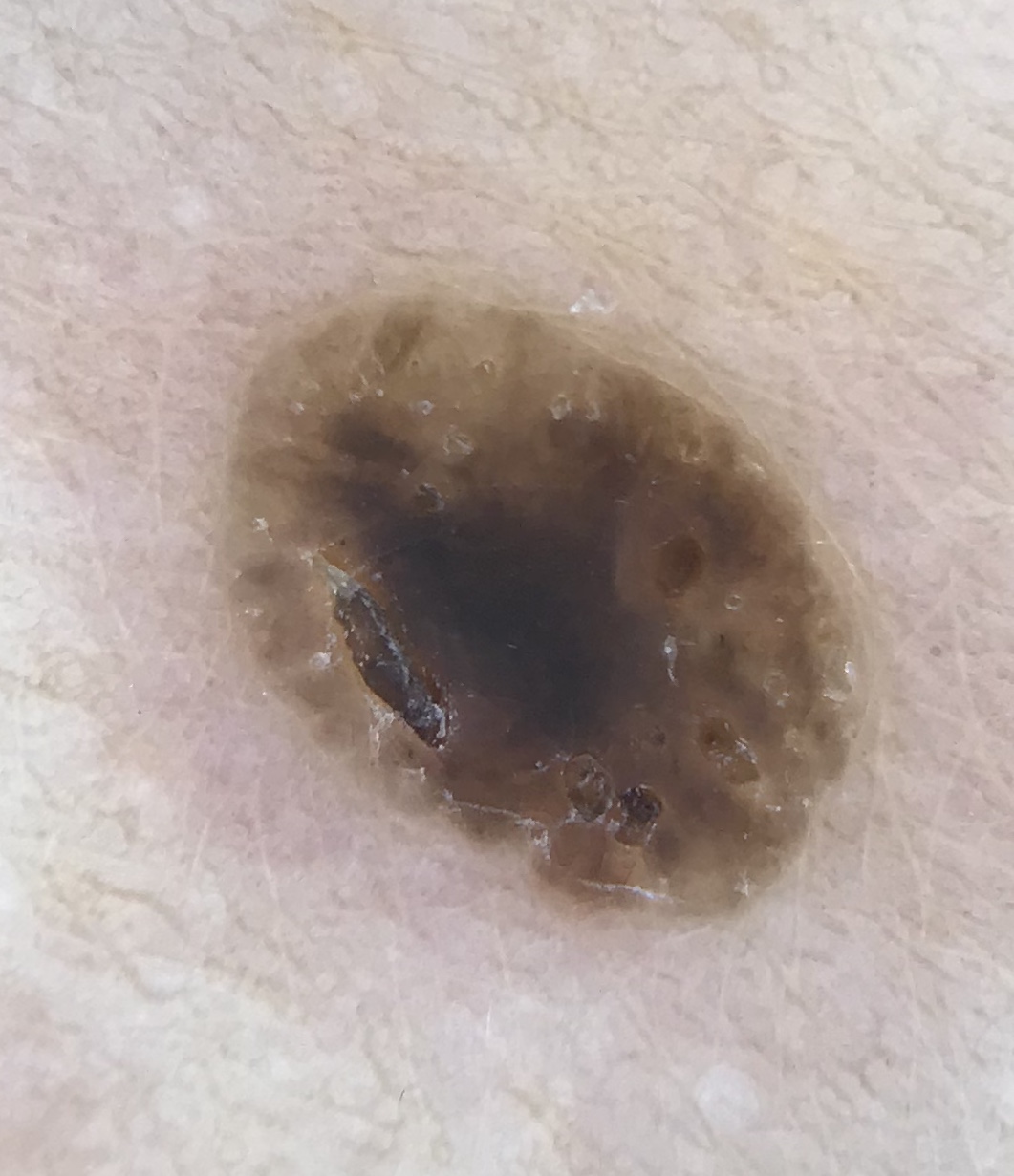{"image": "dermatoscopy", "diagnosis": {"name": "seborrheic keratosis", "code": "sk", "malignancy": "benign", "super_class": "non-melanocytic", "confirmation": "expert consensus"}}